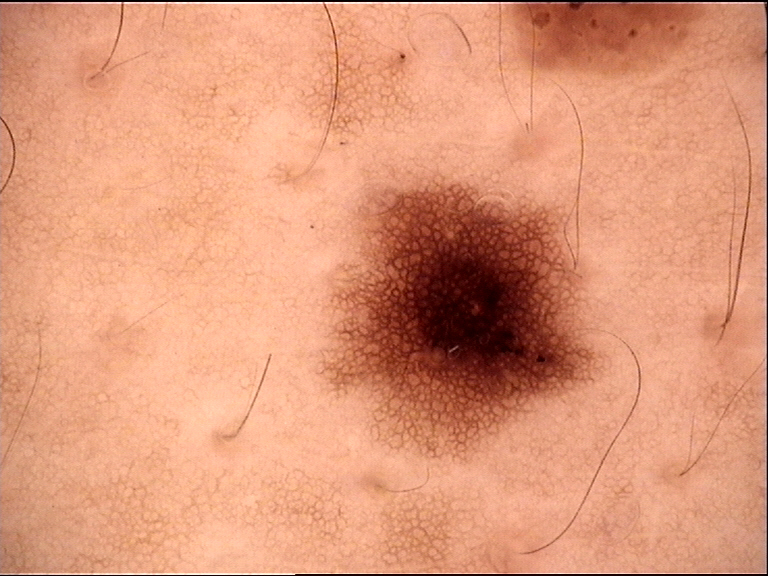Findings:
A dermoscopic photograph of a skin lesion. The morphology is that of a banal lesion.
Impression:
The diagnosis was a junctional nevus.